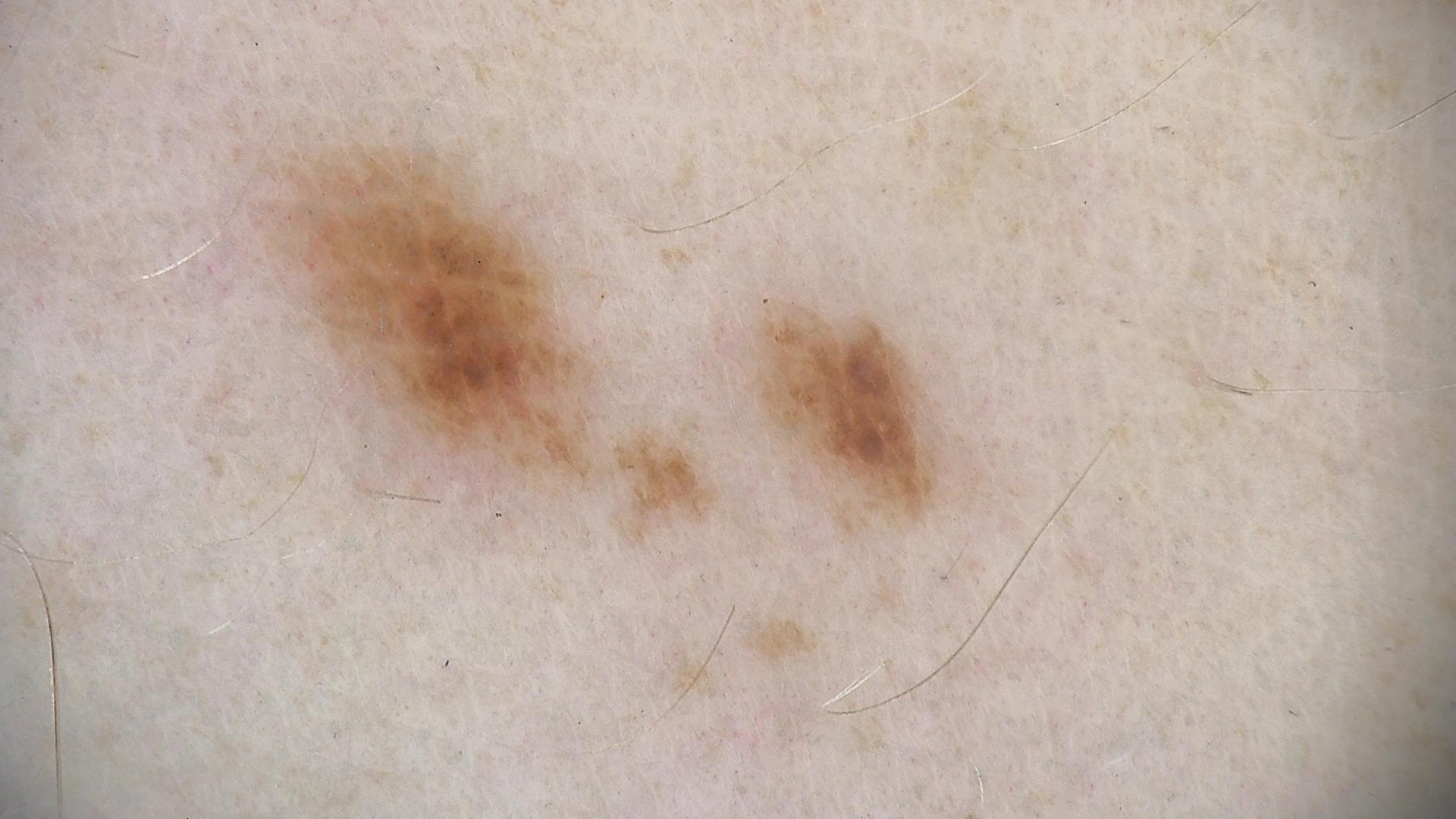Consistent with a dysplastic junctional nevus.